A skin lesion imaged with a dermatoscope.
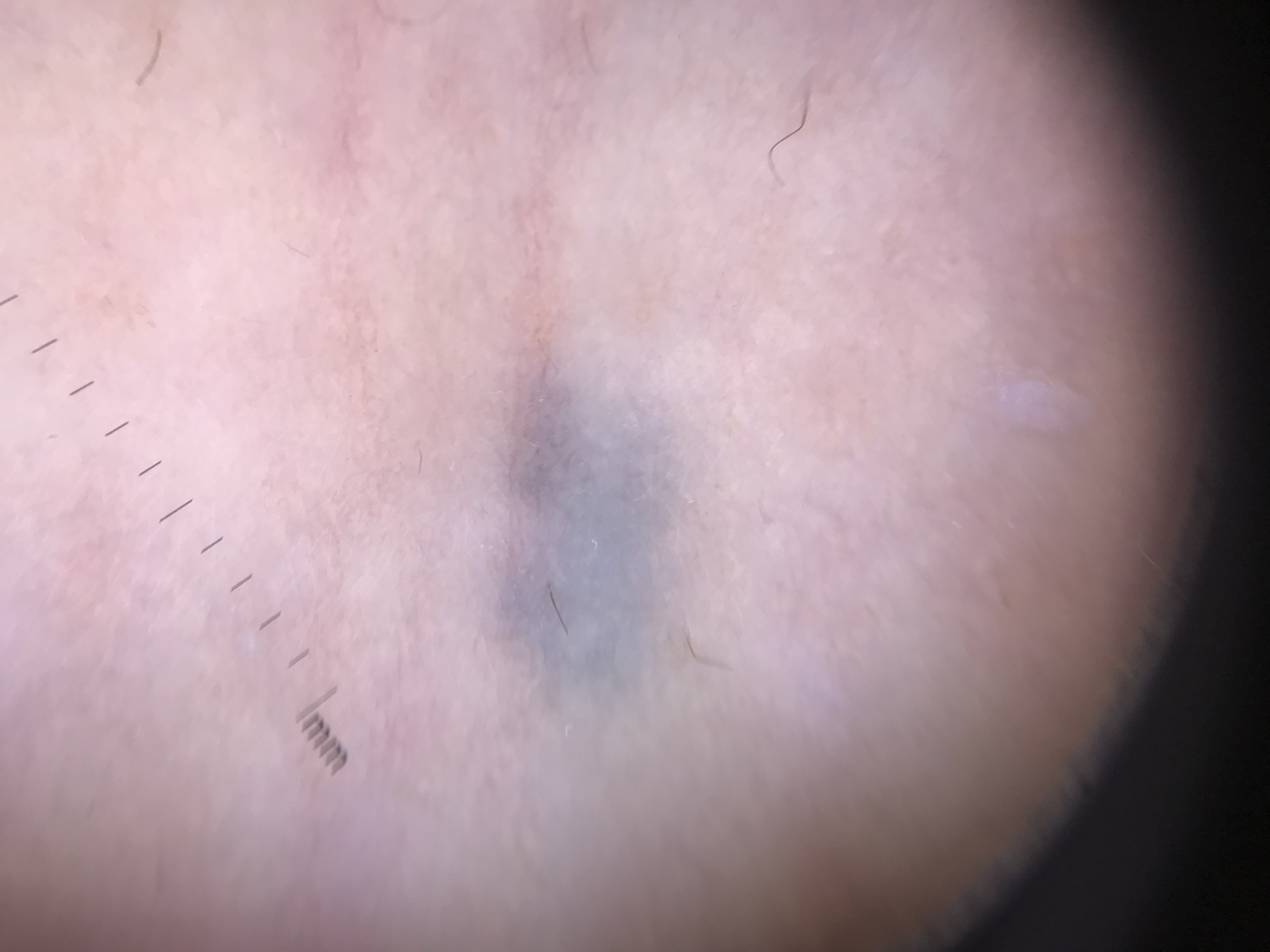Conclusion:
Consistent with a dermal lesion — a blue nevus.